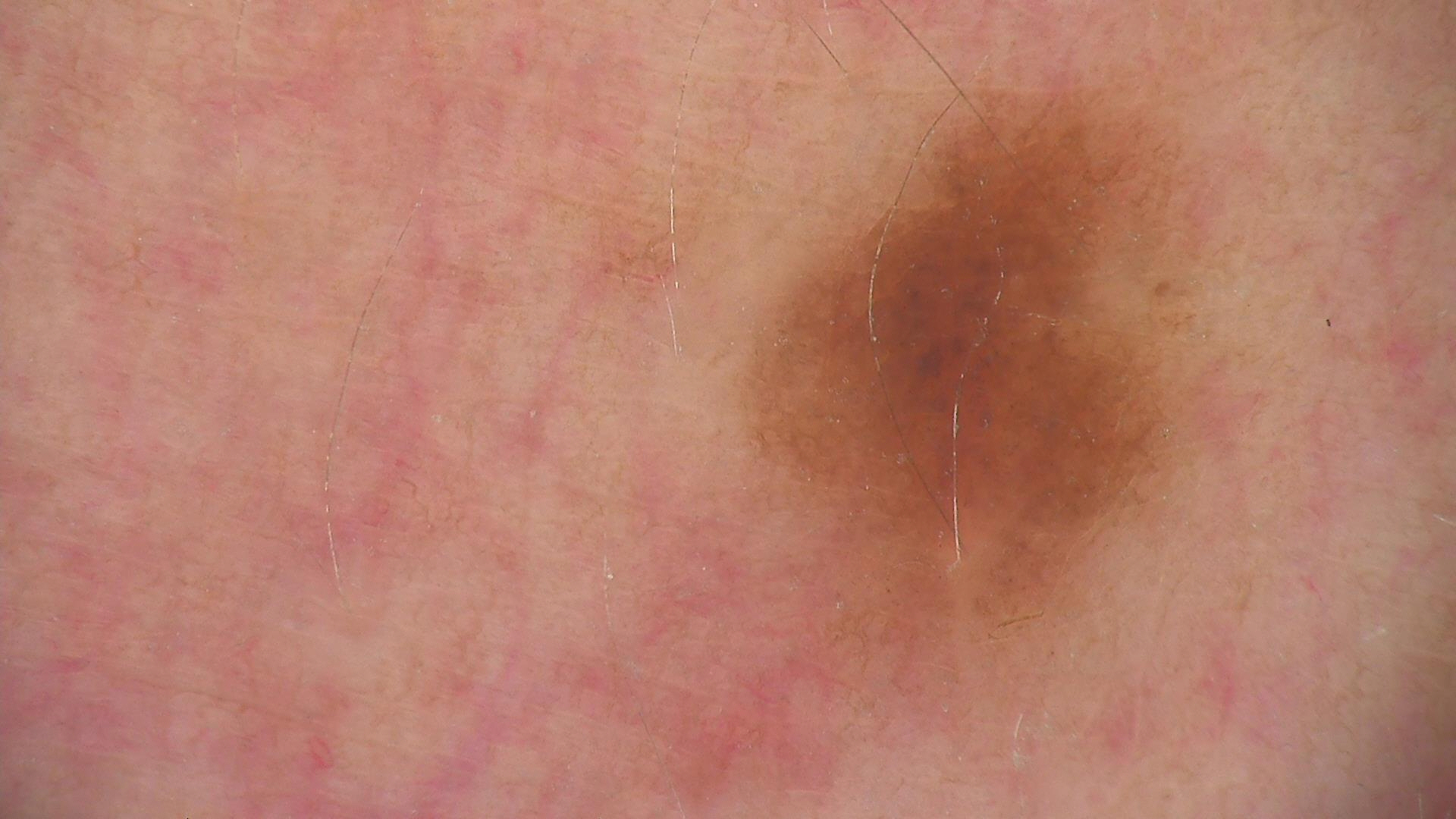Classified as a dysplastic junctional nevus.